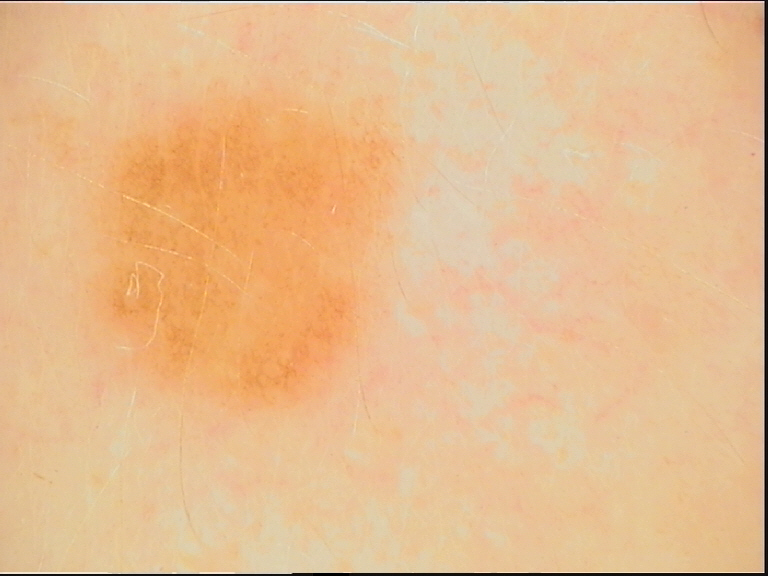A dermoscopic image of a skin lesion. This is a banal lesion. Diagnosed as a junctional nevus.